A dermoscopy image of a single skin lesion.
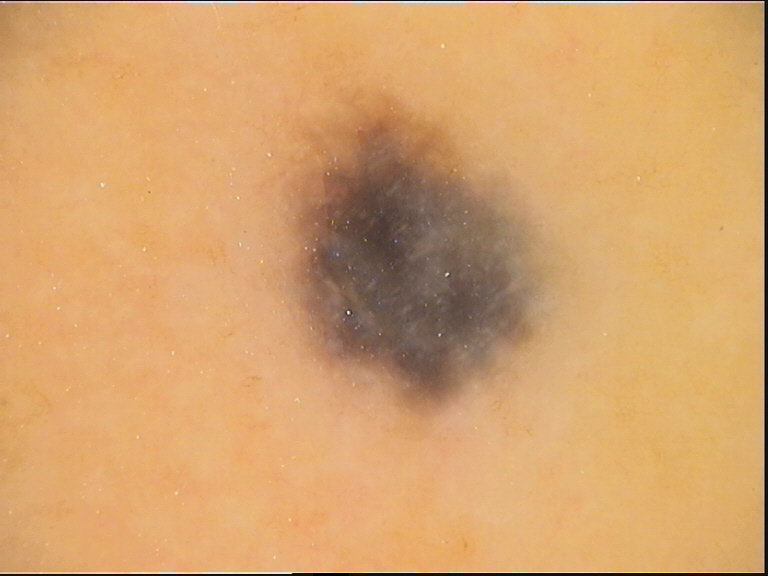Conclusion:
Consistent with a banal lesion — a blue nevus.